The arm is involved · the lesion is described as fluid-filled · close-up view · the condition has been present for about one day · FST III; lay graders estimated a MST of 3 · the patient described the issue as acne — 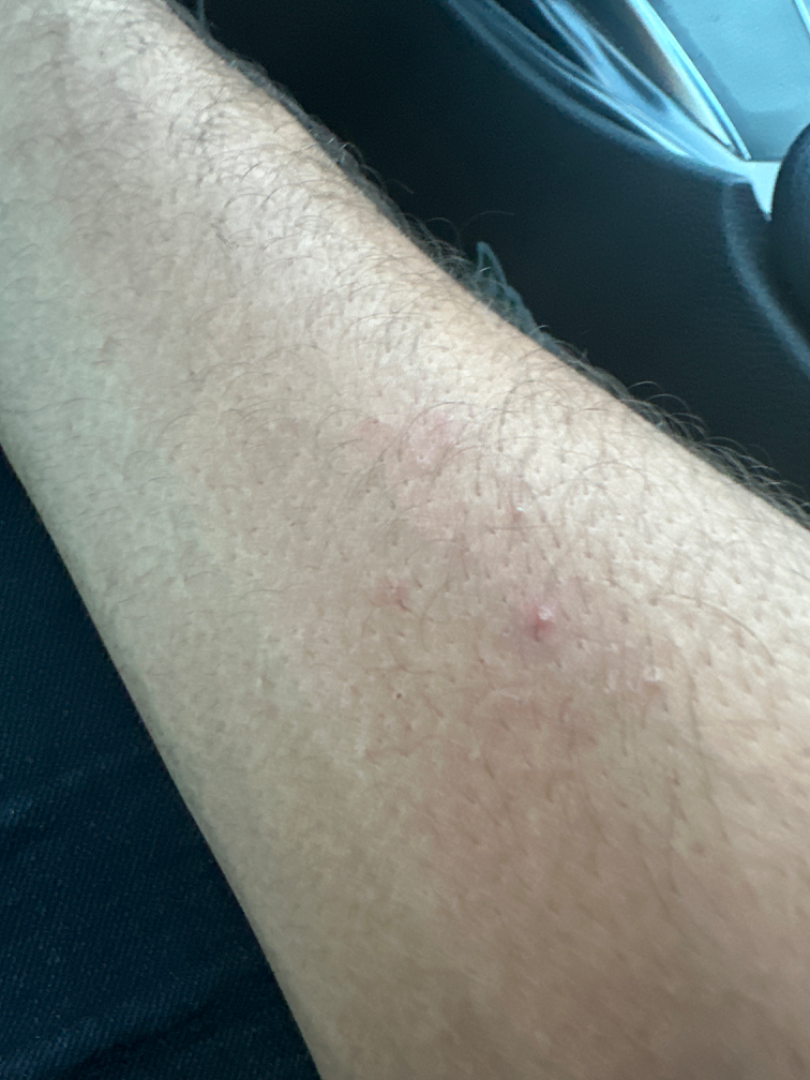The leading impression is Eczema.